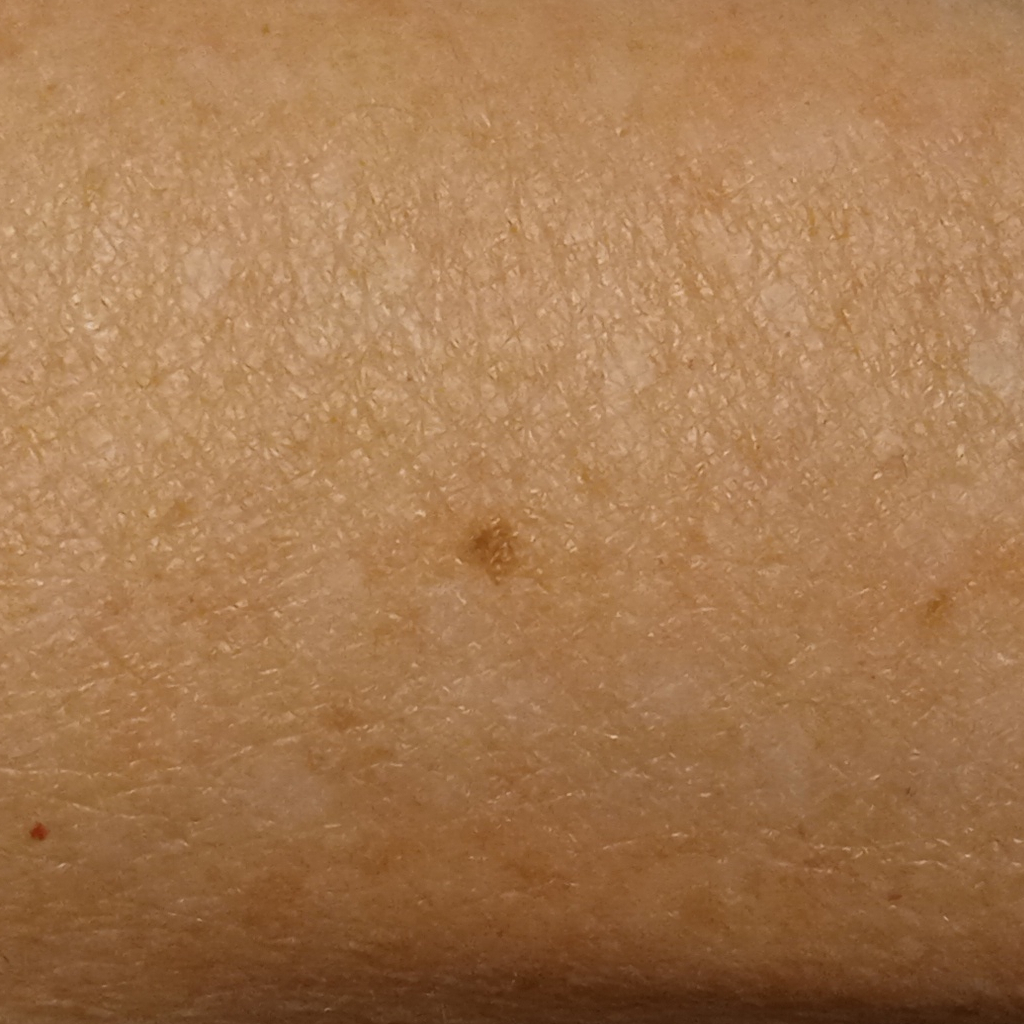diagnosis:
  name: melanocytic nevus
  malignancy: benign